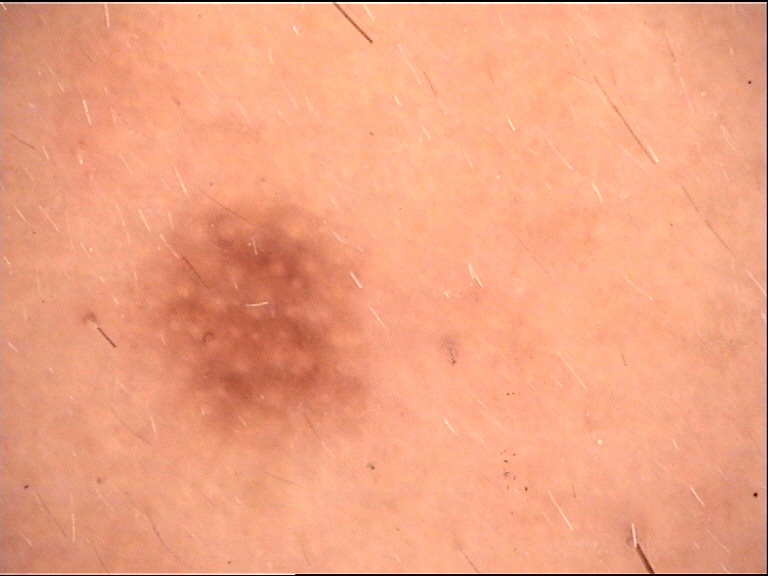imaging = dermoscopy; classification = banal, compound; diagnosis = Miescher nevus (expert consensus).